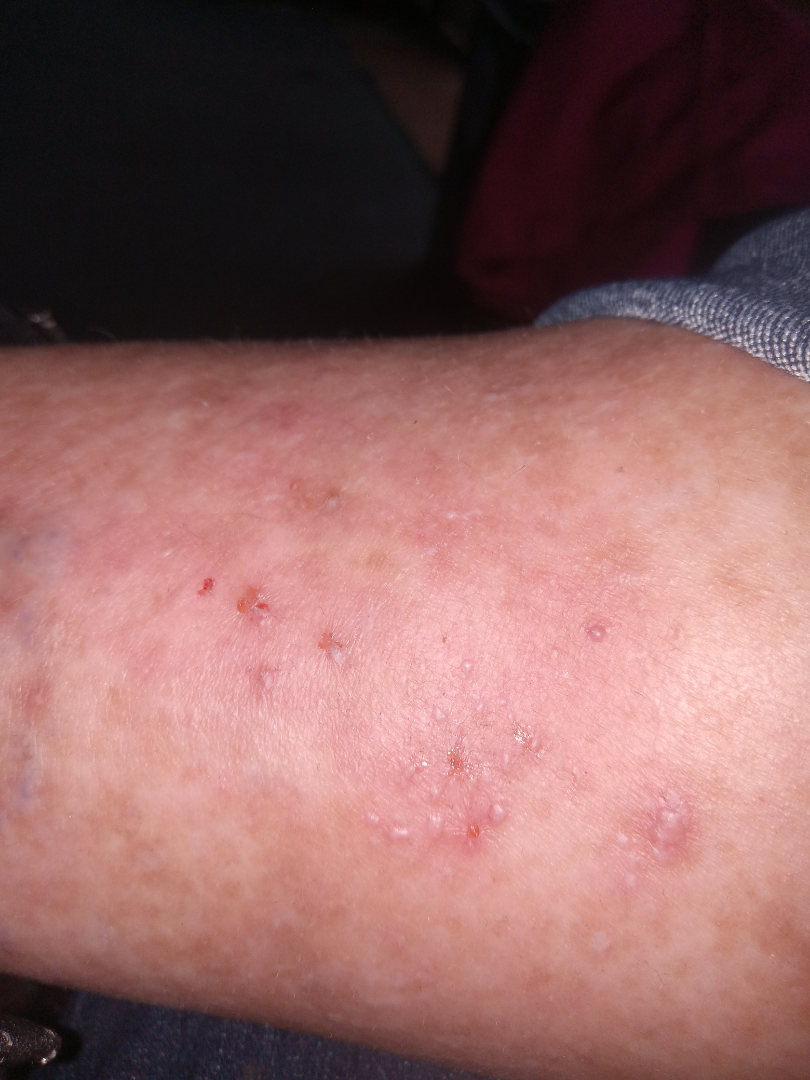lesion texture: fluid-filled and raised or bumpy
framing: close-up
symptoms: burning, bothersome appearance, pain and itching
site: leg
history: about one day
self-categorized as: a rash
associated systemic symptoms: none reported
differential: the impression was split between Herpes Zoster, Stasis Dermatitis and Bullous Pemphigoid